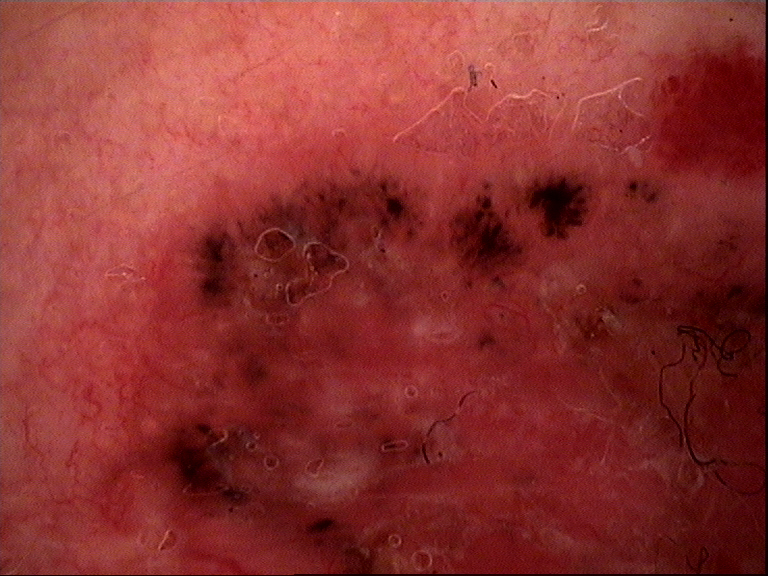Conclusion:
Biopsy-confirmed as a basal cell carcinoma.